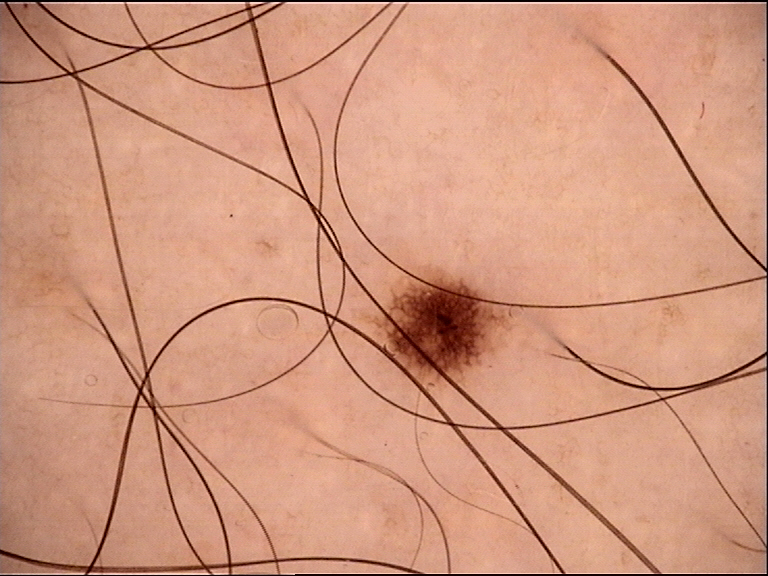{"diagnosis": {"name": "dysplastic junctional nevus", "code": "jd", "malignancy": "benign", "super_class": "melanocytic", "confirmation": "expert consensus"}}